A dermatoscopic image of a skin lesion:
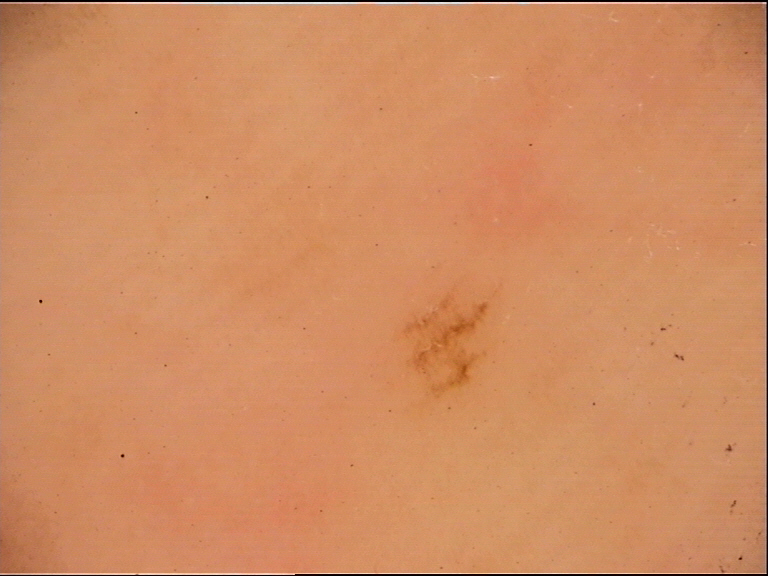label=acral junctional nevus (expert consensus).